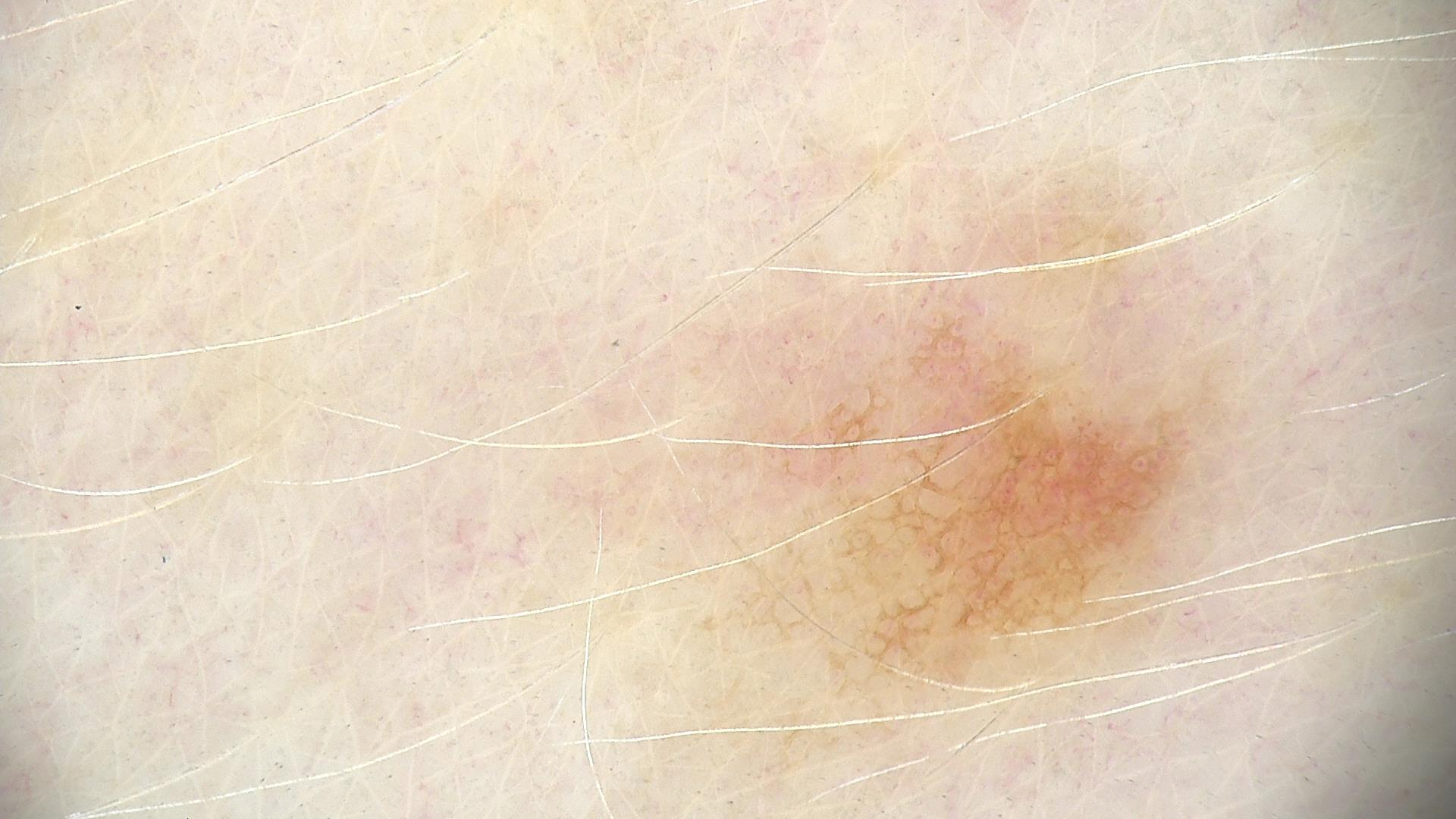{"image": "dermatoscopy", "lesion_type": {"main_class": "banal", "pattern": "junctional"}, "diagnosis": {"name": "junctional nevus", "code": "jb", "malignancy": "benign", "super_class": "melanocytic", "confirmation": "expert consensus"}}